A dermoscopic close-up of a skin lesion.
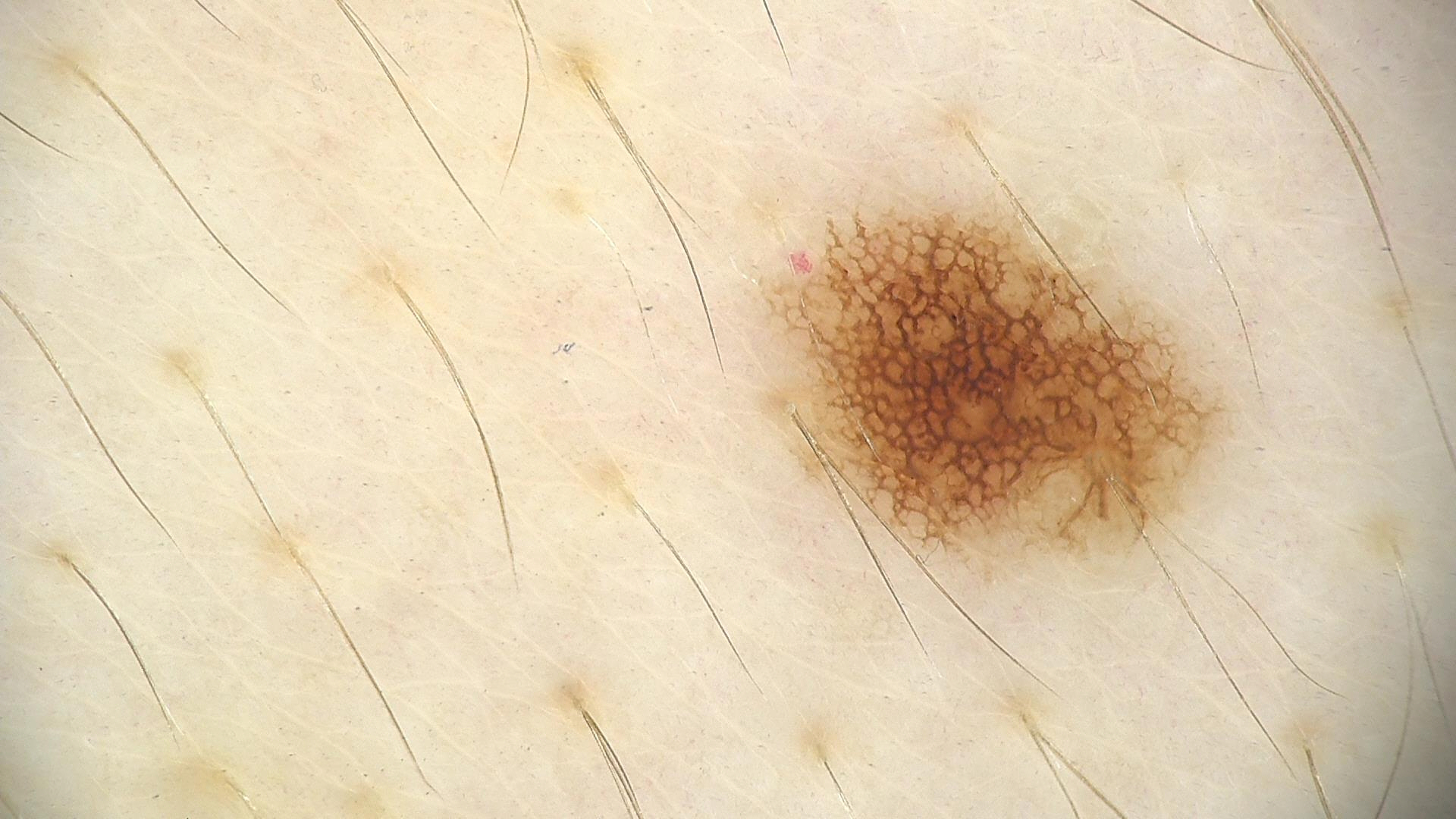Impression: Consistent with a benign lesion — a dysplastic junctional nevus.